This image was taken at an angle:
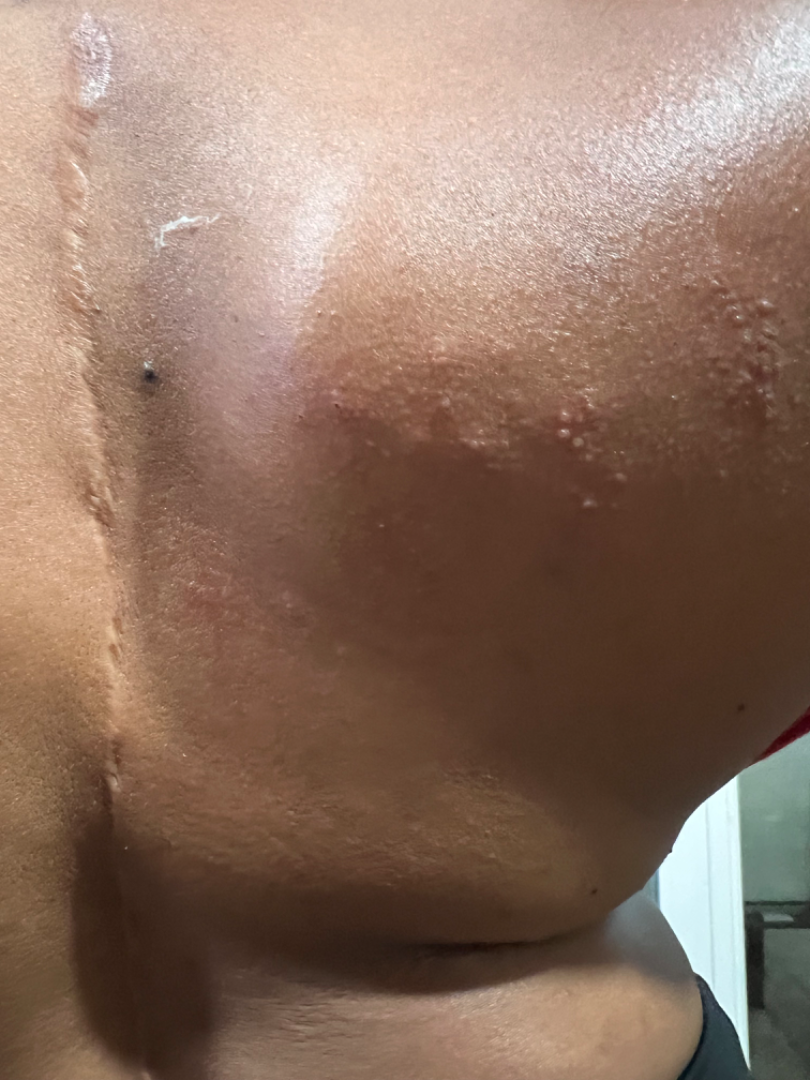Impression: The dermatologist could not determine a likely condition from the photograph alone.